A dermoscopic close-up of a skin lesion:
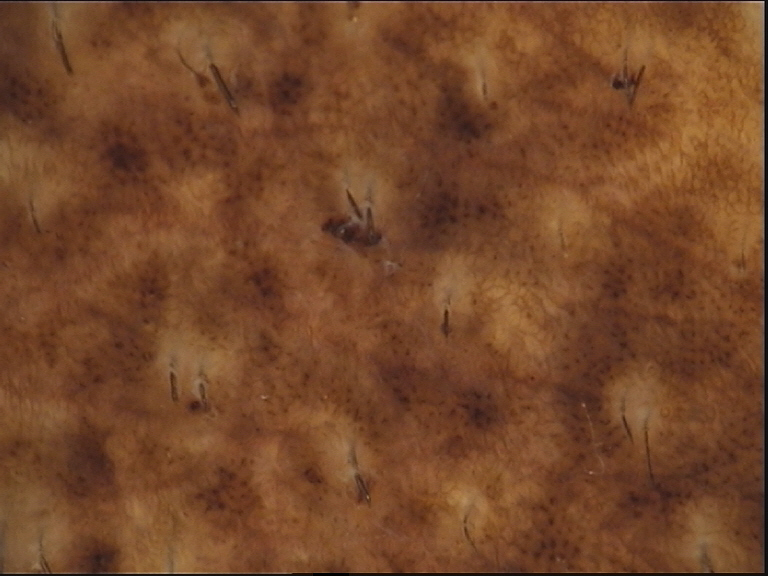This is a banal lesion. The diagnosis was a congenital compound nevus.